A dermoscopic photograph of a skin lesion.
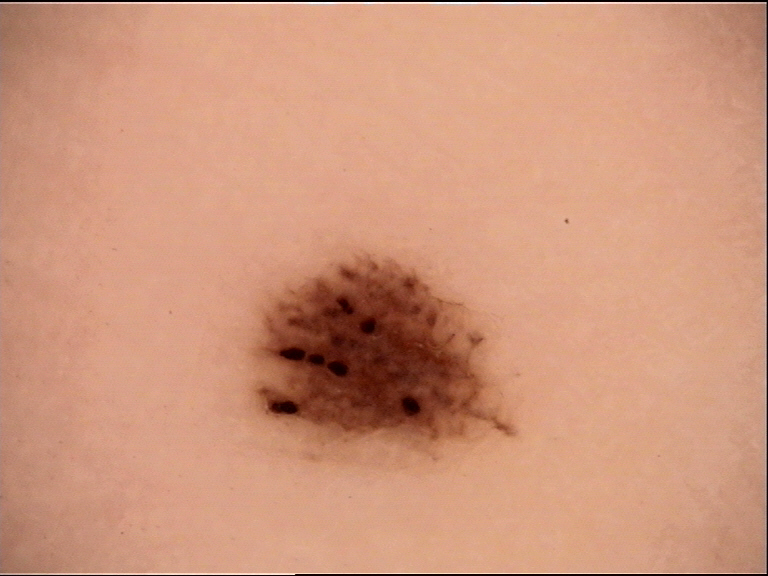<dermoscopy>
<diagnosis>
<name>acral dysplastic junctional nevus</name>
<code>ajd</code>
<malignancy>benign</malignancy>
<super_class>melanocytic</super_class>
<confirmation>expert consensus</confirmation>
</diagnosis>
</dermoscopy>